The patient is Fitzpatrick phototype III. A clinical close-up photograph of a skin lesion. A male subject 49 years of age. History notes prior skin cancer (patient or family), pesticide exposure, no prior malignancy (patient or family), and no tobacco use:
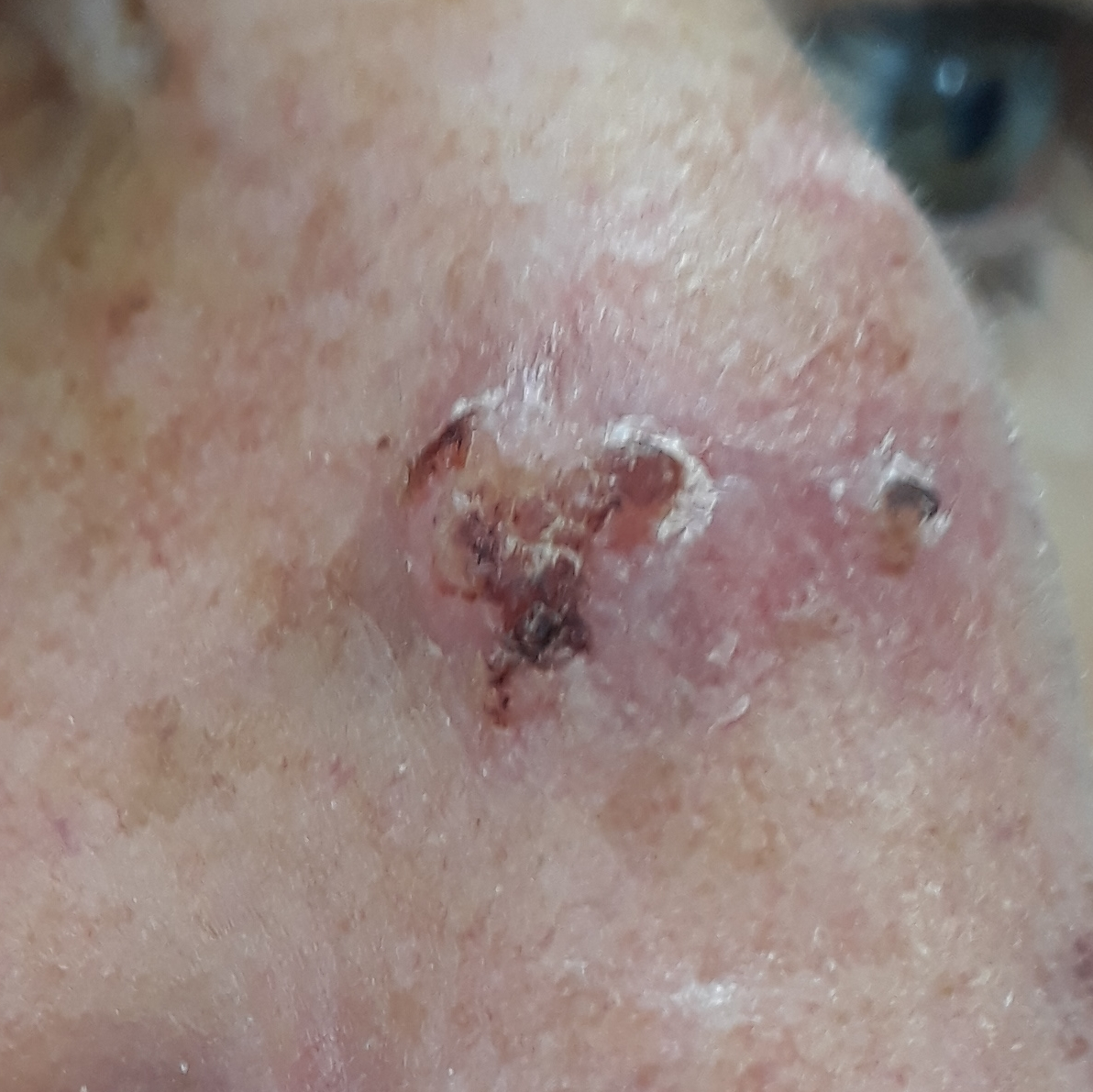Located on the nose. The lesion measures 14 × 9 mm. The patient describes that the lesion has grown, hurts, is elevated, itches, and has bled. On biopsy, the diagnosis was a malignant skin lesion — a basal cell carcinoma.